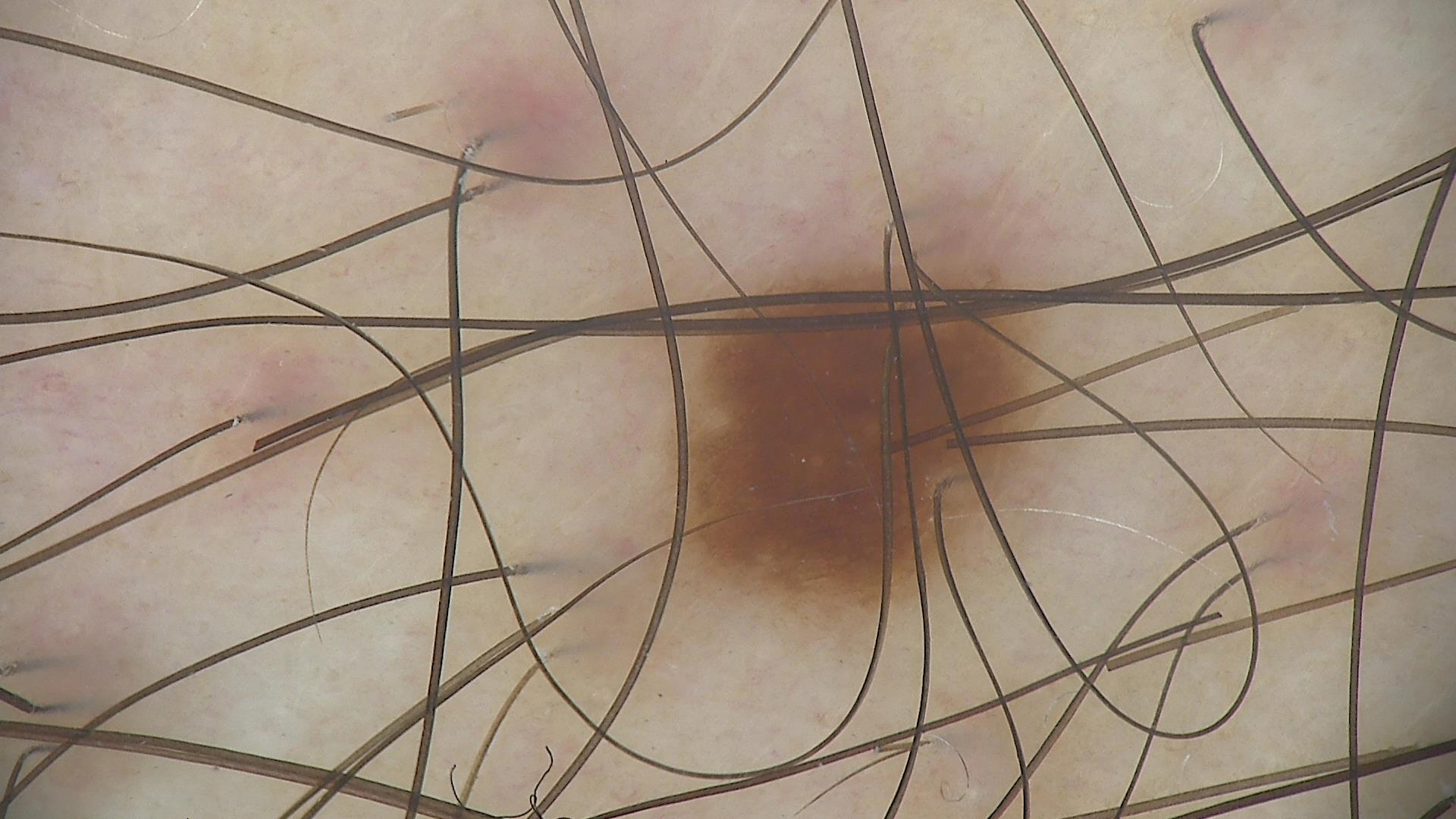{"diagnosis": {"name": "dysplastic junctional nevus", "code": "jd", "malignancy": "benign", "super_class": "melanocytic", "confirmation": "expert consensus"}}